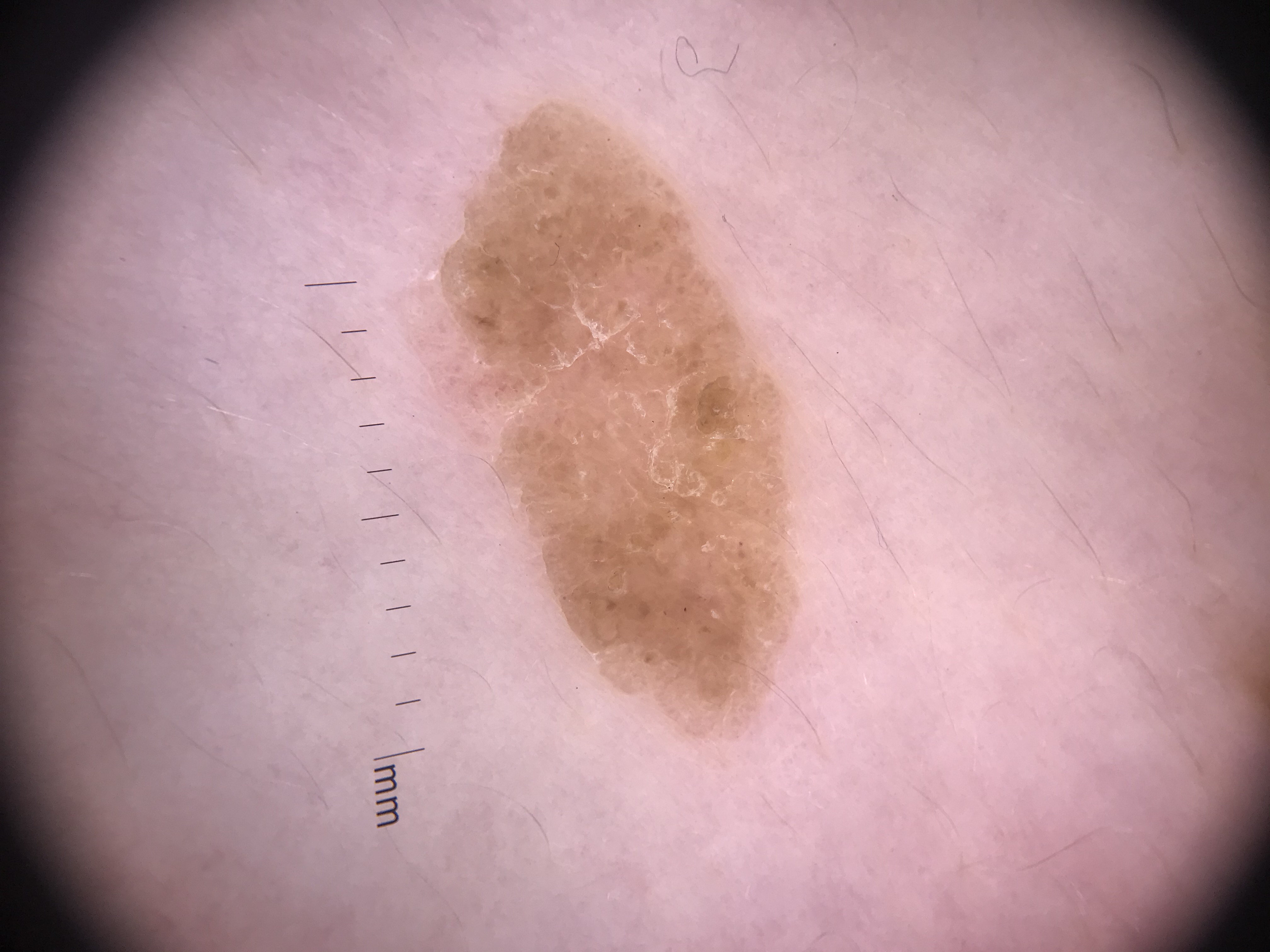Findings:
- lesion type · keratinocytic
- diagnosis · seborrheic keratosis (expert consensus)